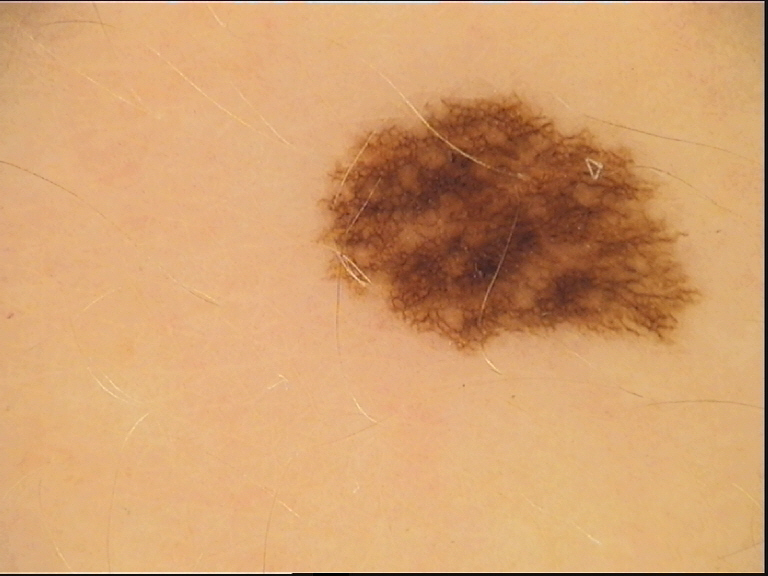A skin lesion imaged with a dermatoscope. The diagnosis was a benign lesion — a dysplastic junctional nevus.